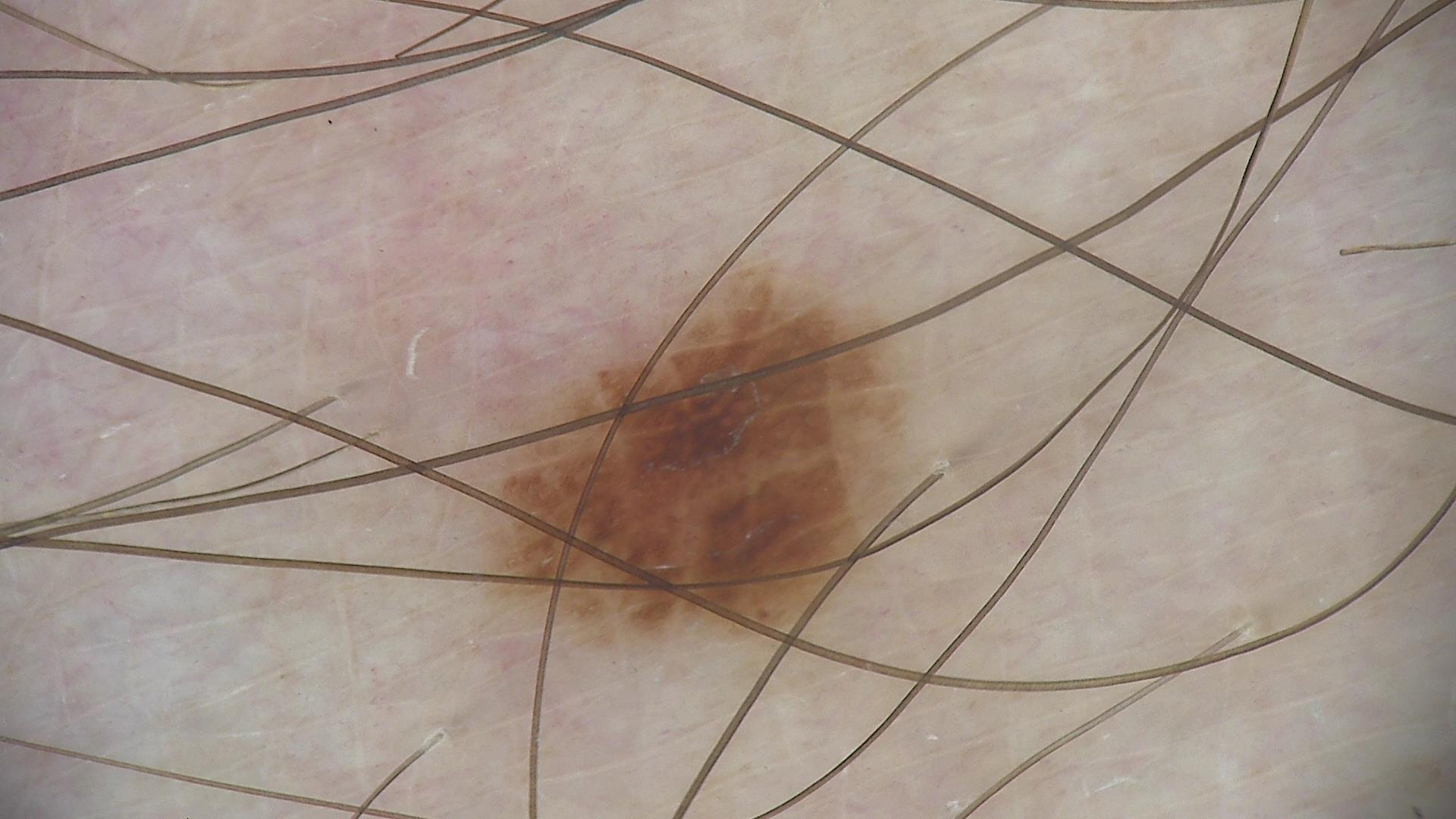{"diagnosis": {"name": "dysplastic junctional nevus", "code": "jd", "malignancy": "benign", "super_class": "melanocytic", "confirmation": "expert consensus"}}